The photograph was taken at an angle; located on the arm; the subject is 18–29, female — 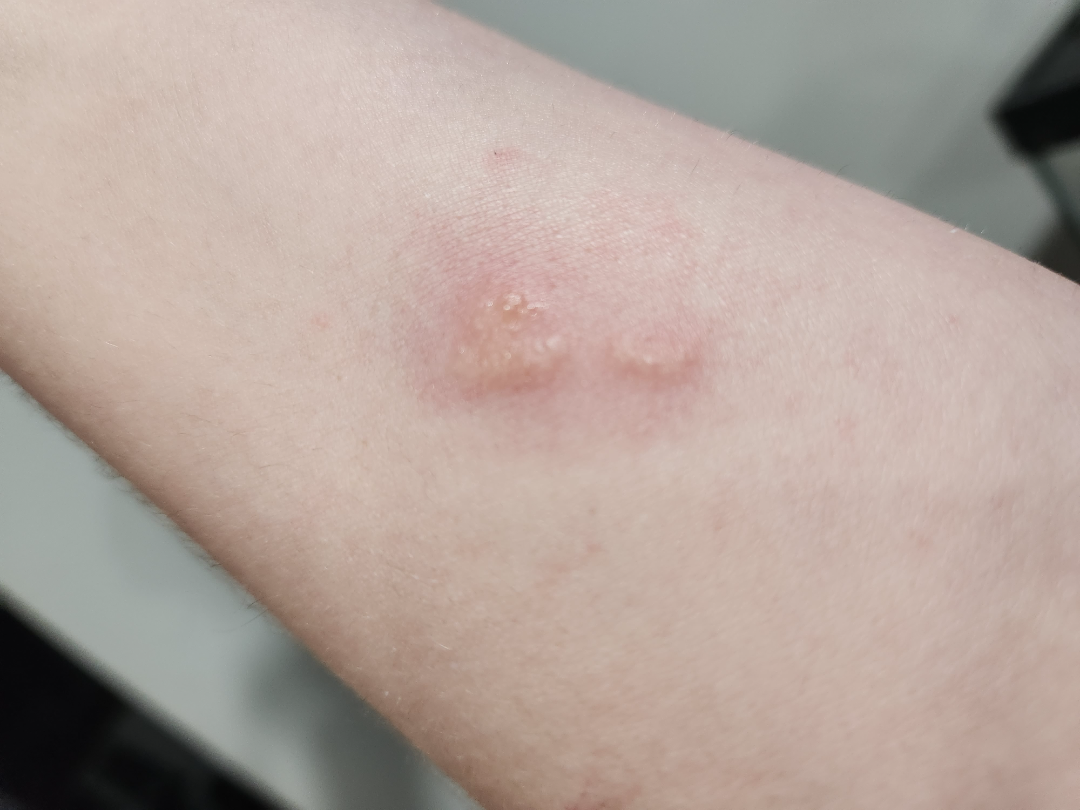The patient indicates itching.
The patient indicates the condition has been present for about one day.
The patient considered this a rash.
On remote dermatologist review, Blister (0.55); Herpes Simplex (0.27); Herpes Zoster (0.18).